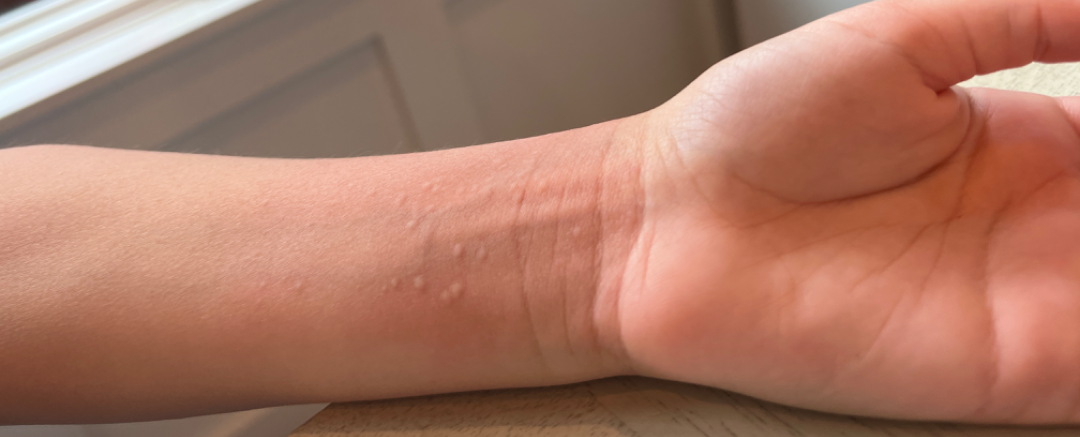{
  "patient_category": "a rash",
  "shot_type": "at an angle",
  "body_site": "arm",
  "texture": "raised or bumpy",
  "symptoms": "itching",
  "duration": "about one day",
  "differential": {
    "leading": [
      "Urticaria"
    ],
    "considered": [
      "Verruca vulgaris",
      "Allergic Contact Dermatitis"
    ]
  }
}